A dermoscopic photograph of a skin lesion: 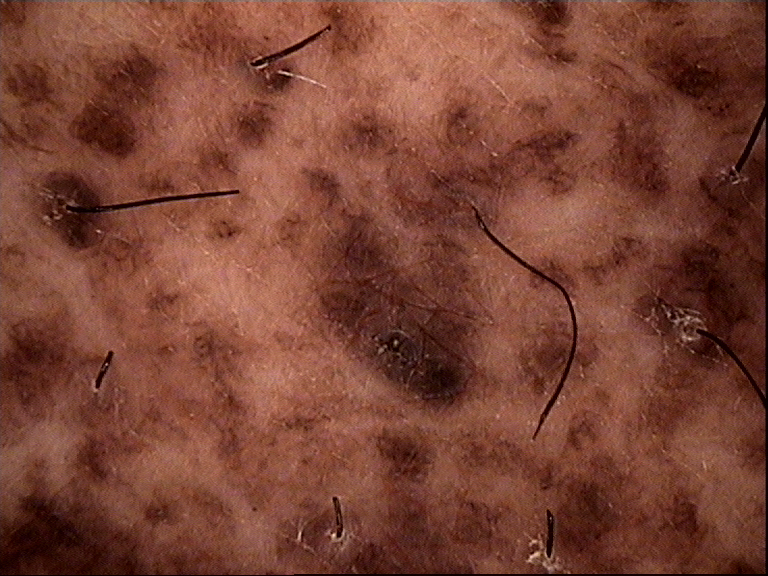Conclusion:
The diagnostic label was a banal lesion — a congenital compound nevus.